A subject aged 10. A clinical close-up photograph of a skin lesion — 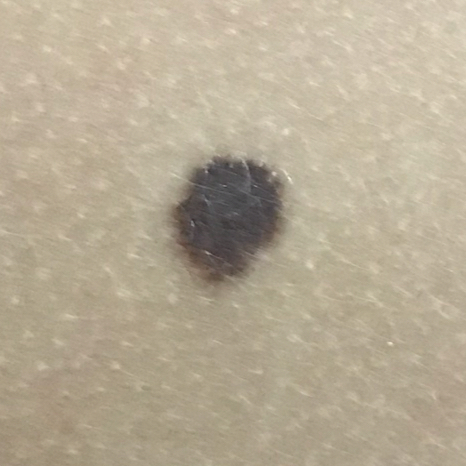{"lesion_location": "the back", "symptoms": {"absent": ["pain", "itching"]}, "diagnosis": {"name": "nevus", "code": "NEV", "malignancy": "benign", "confirmation": "clinical consensus"}}